The photograph is a close-up of the affected area; the back of the hand is involved; the contributor is male:
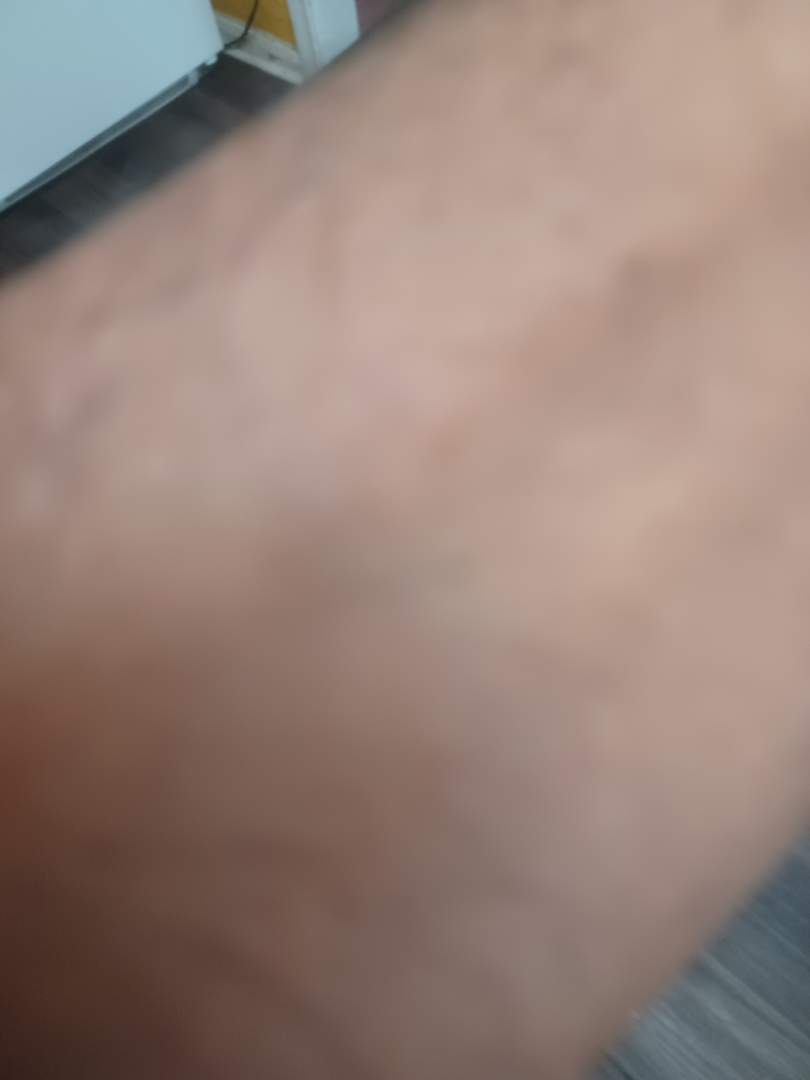assessment = indeterminate from the photograph; symptom duration = less than one week; described texture = raised or bumpy.